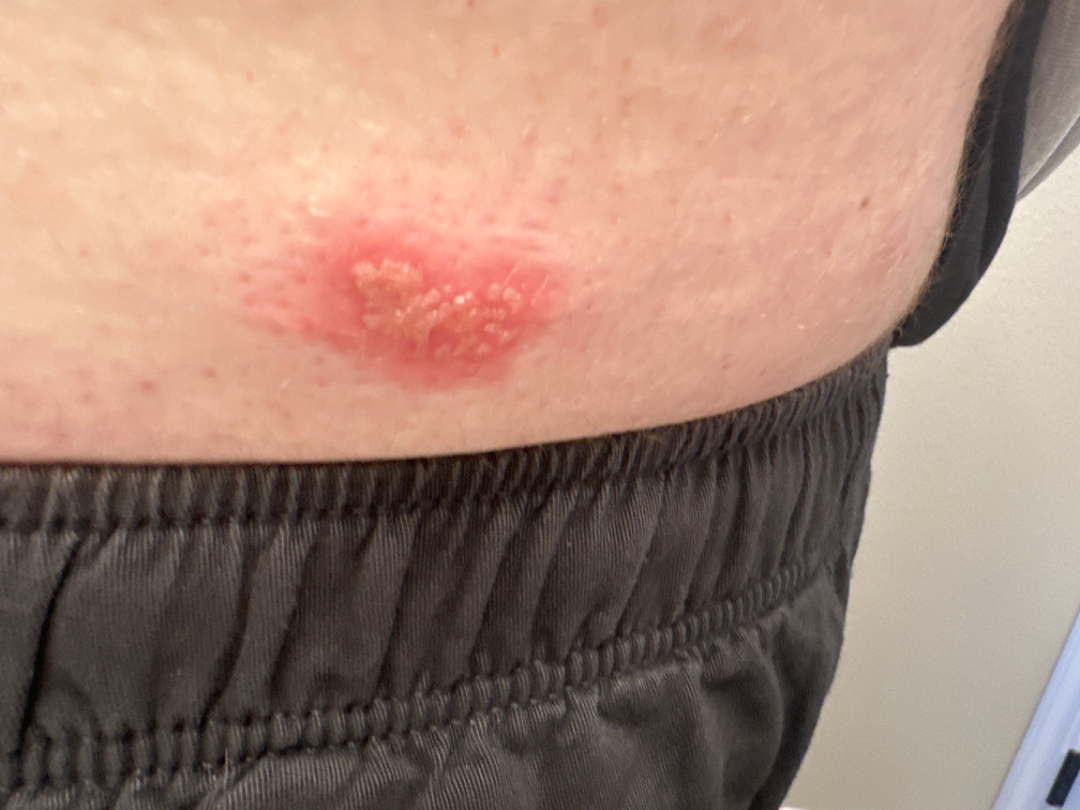image framing: at a distance
contributor: male, age 18–29
self-categorized as: a rash
lesion texture: raised or bumpy
location: back of the torso
symptoms: pain
present for: less than one week
impression: Herpes Simplex (weight 0.62); Lymphangioma (weight 0.19); Herpes Zoster (weight 0.19)